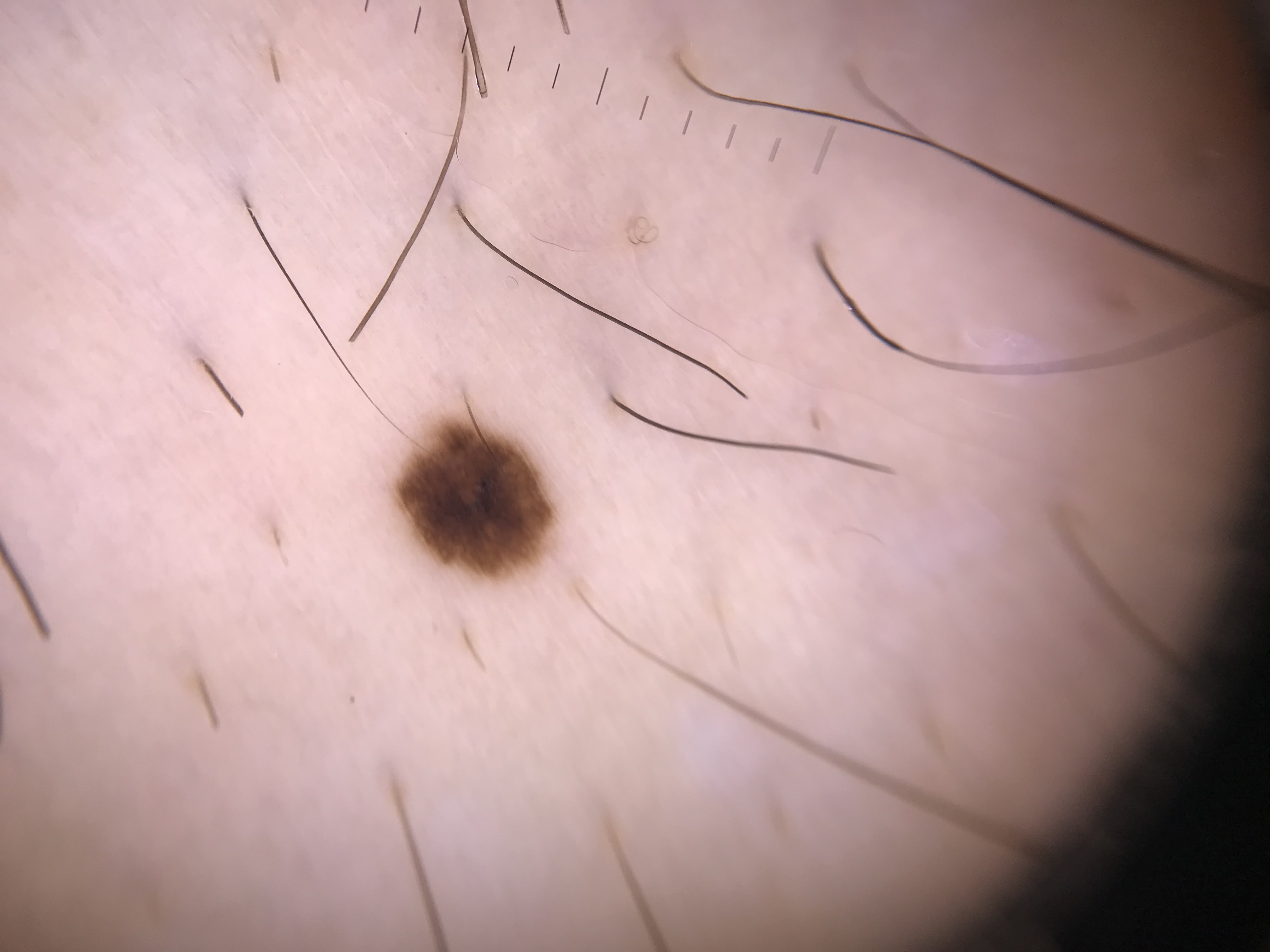class: dysplastic junctional nevus (expert consensus).